A dermoscopic view of a skin lesion — 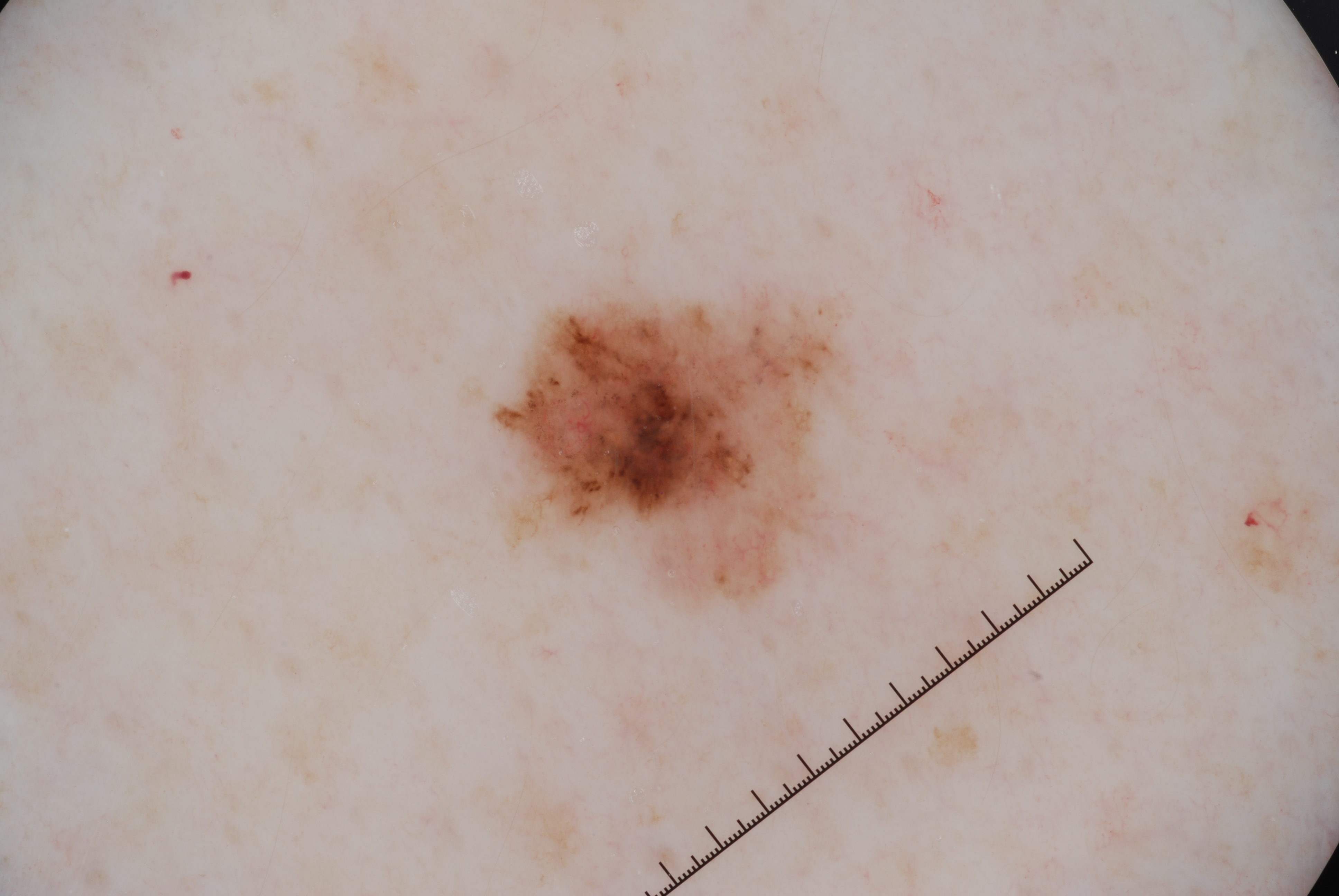The lesion takes up about 6% of the image. On dermoscopy, the lesion shows pigment network and milia-like cysts; no streaks or negative network. As (left, top, right, bottom), lesion location: (502, 301, 837, 602). Biopsy-confirmed as a melanoma.